A patient 49 years old · a clinical photo of a skin lesion taken with a smartphone: 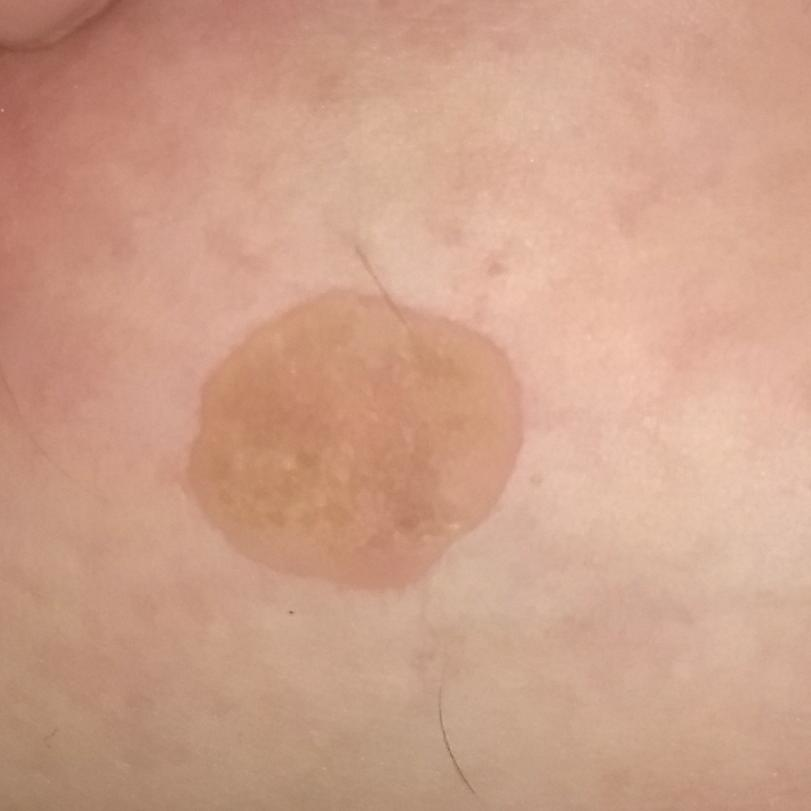Located on the chest.
The patient reports that the lesion itches, has grown, and is elevated, but does not hurt and has not changed.
Diagnosed by dermatologist consensus as a seborrheic keratosis.